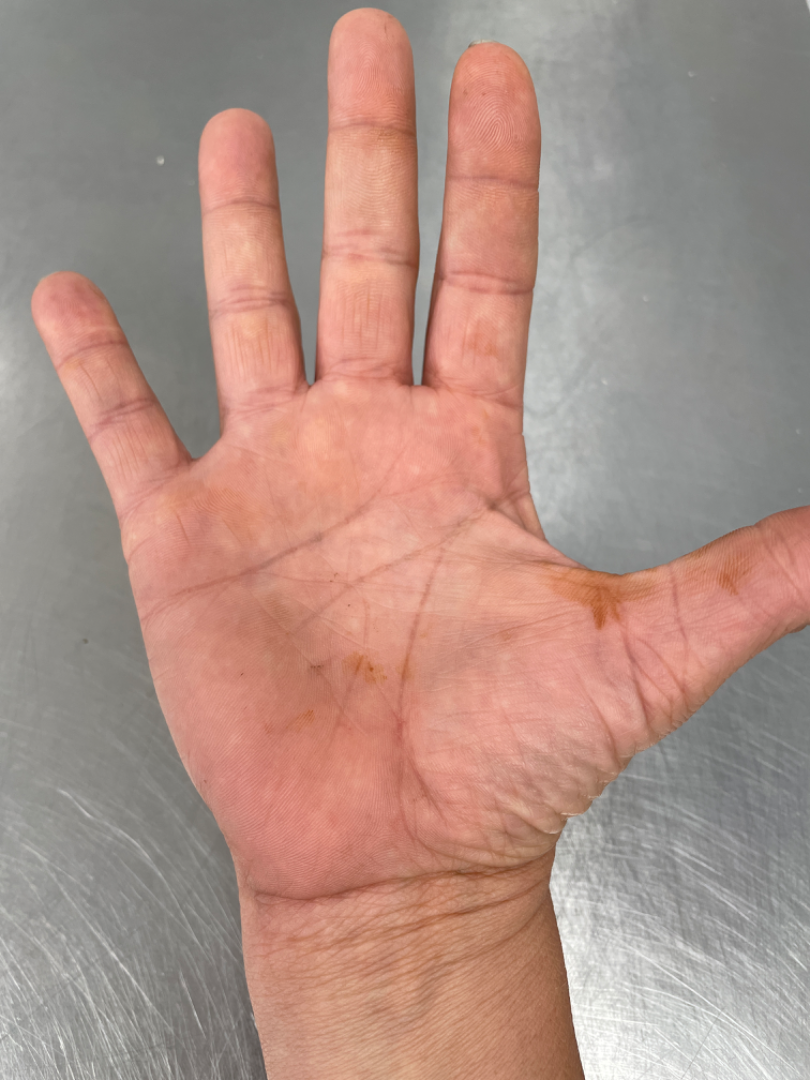{
  "assessment": "could not be assessed",
  "duration": "about one day",
  "body_site": "palm",
  "systemic_symptoms": "none reported",
  "symptoms": "none reported",
  "texture": "flat",
  "shot_type": "at a distance"
}